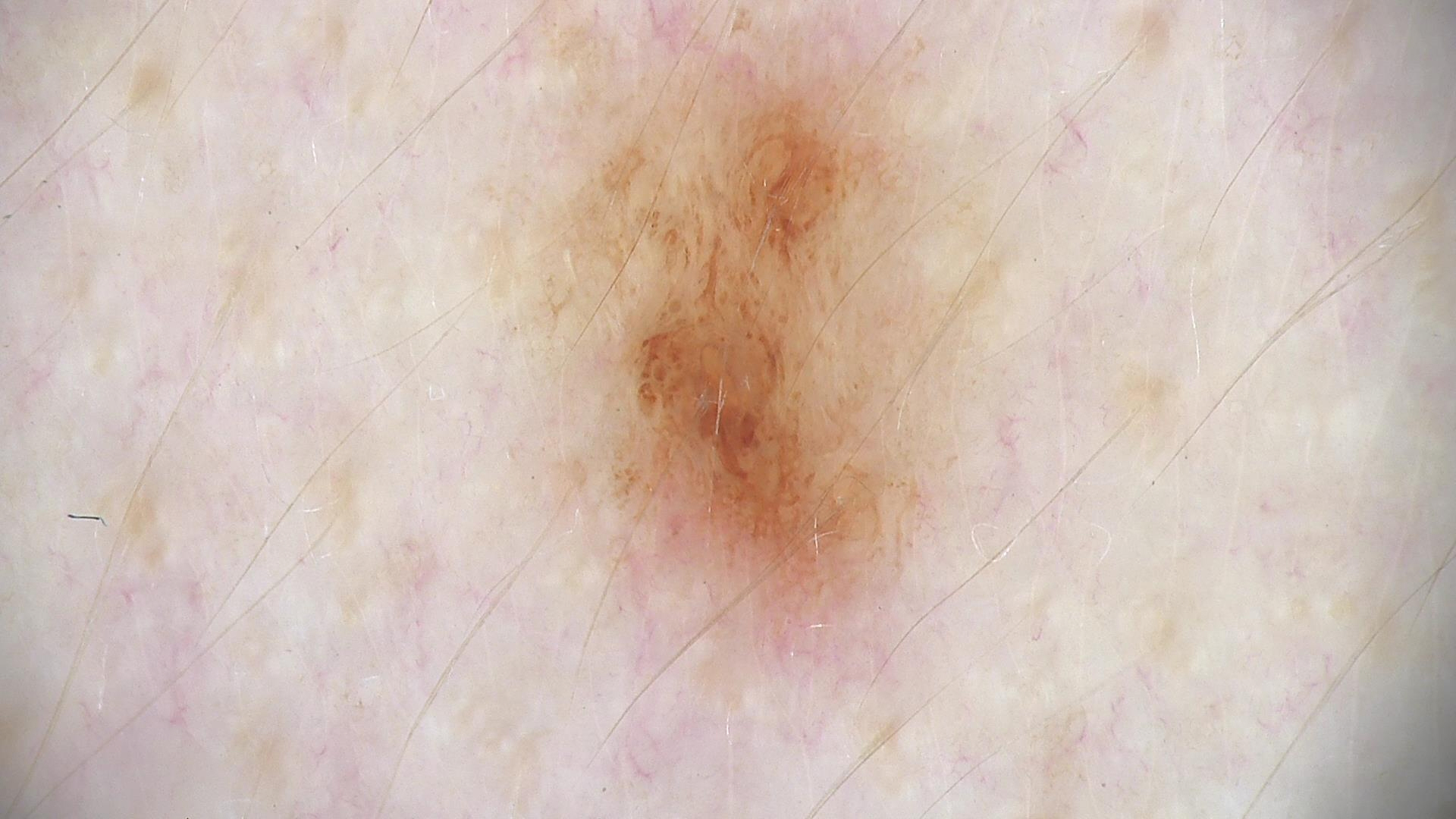A dermoscopic image of a skin lesion.
Labeled as a benign lesion — a dysplastic junctional nevus.